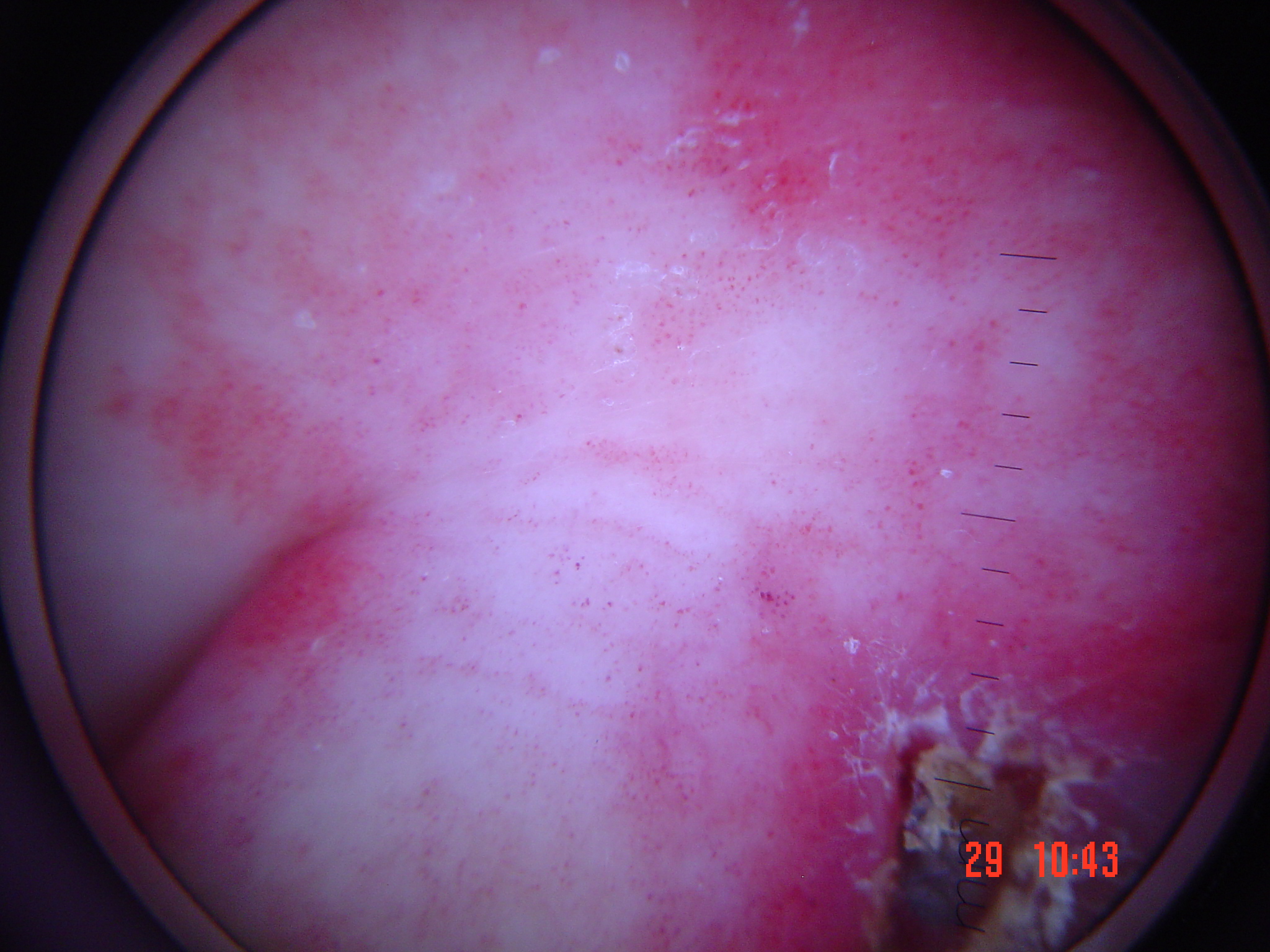The diagnosis was a vascular, benign lesion — a hemangioma.